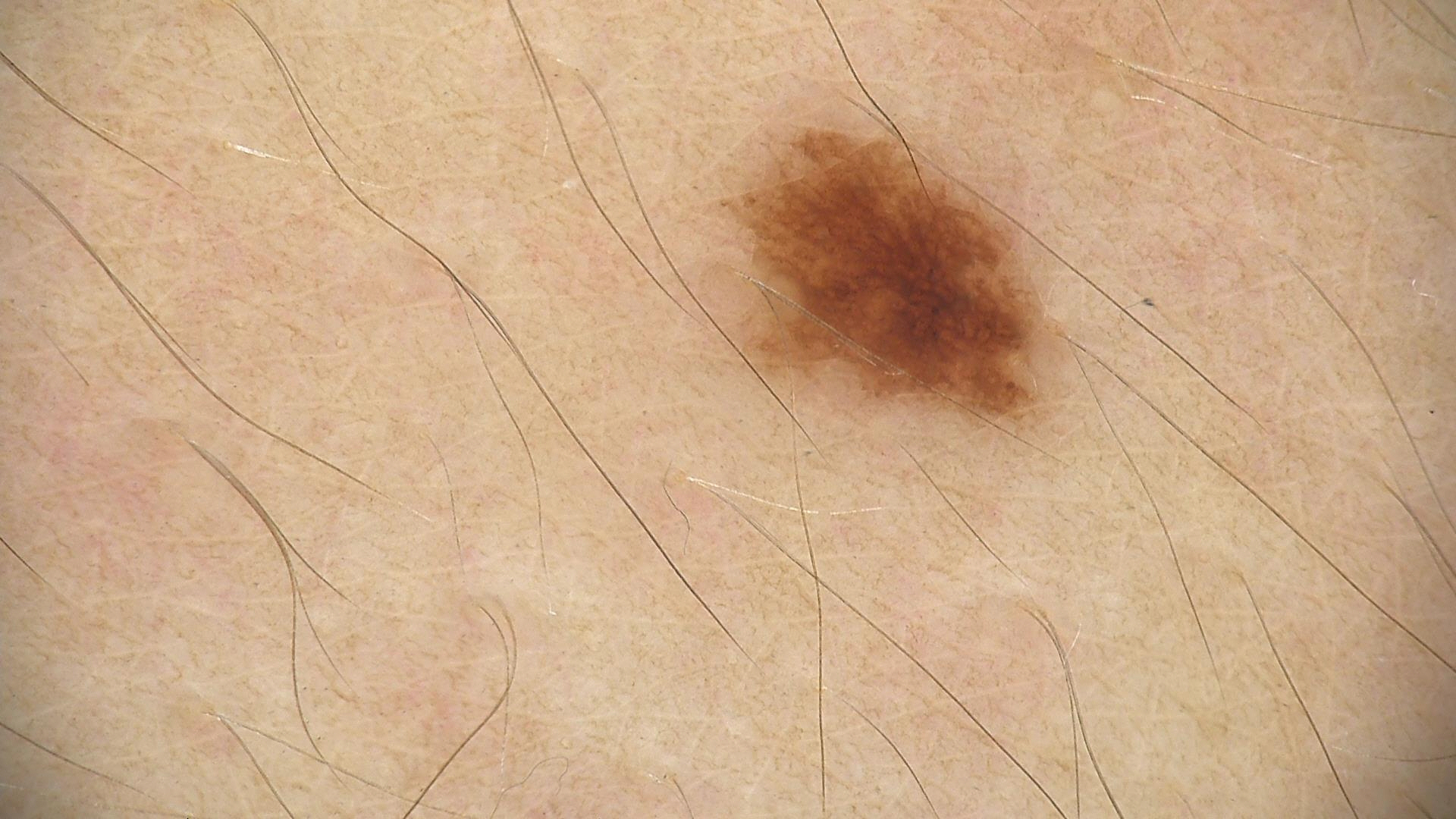Diagnosed as a dysplastic junctional nevus.